A contact-polarized dermoscopy image of a skin lesion.
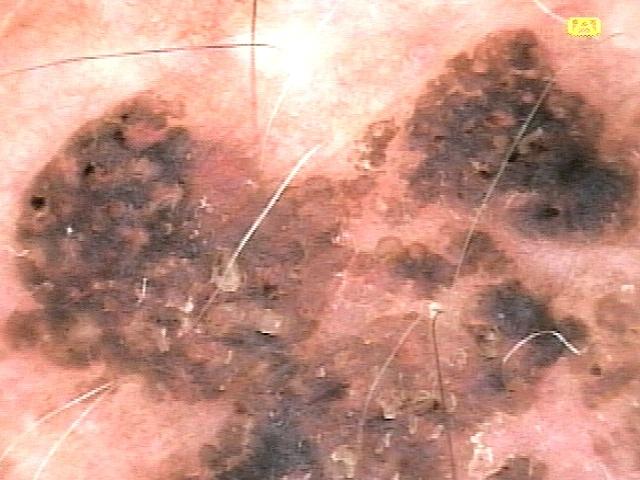The clinical assessment was a seborrheic keratosis.